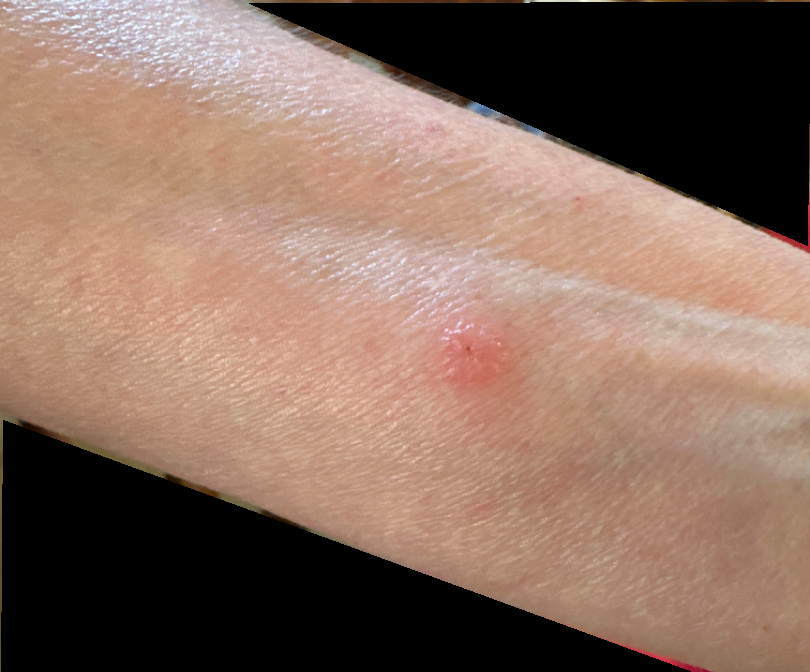assessment: indeterminate from the photograph.